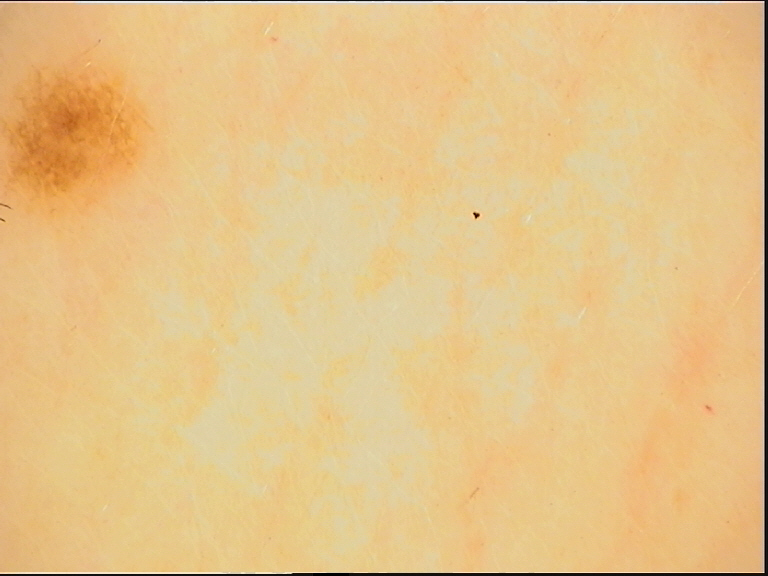{
  "diagnosis": {
    "name": "dysplastic junctional nevus",
    "code": "jd",
    "malignancy": "benign",
    "super_class": "melanocytic",
    "confirmation": "expert consensus"
  }
}